This is a close-up image. Located on the back of the hand.
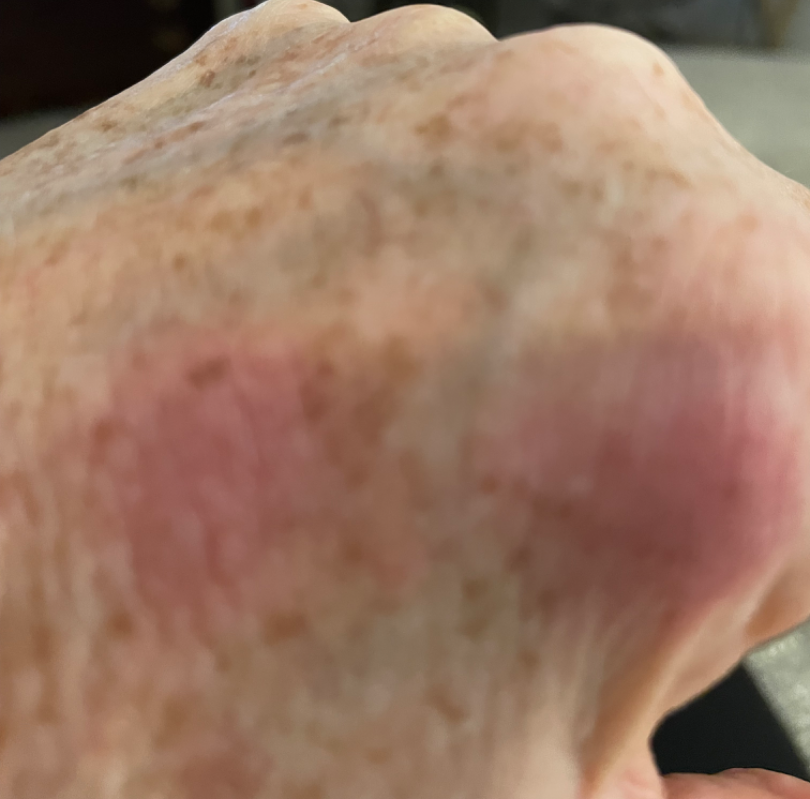The case was indeterminate on photographic review.
The contributor reports the lesion is flat.